A skin lesion imaged with a dermatoscope.
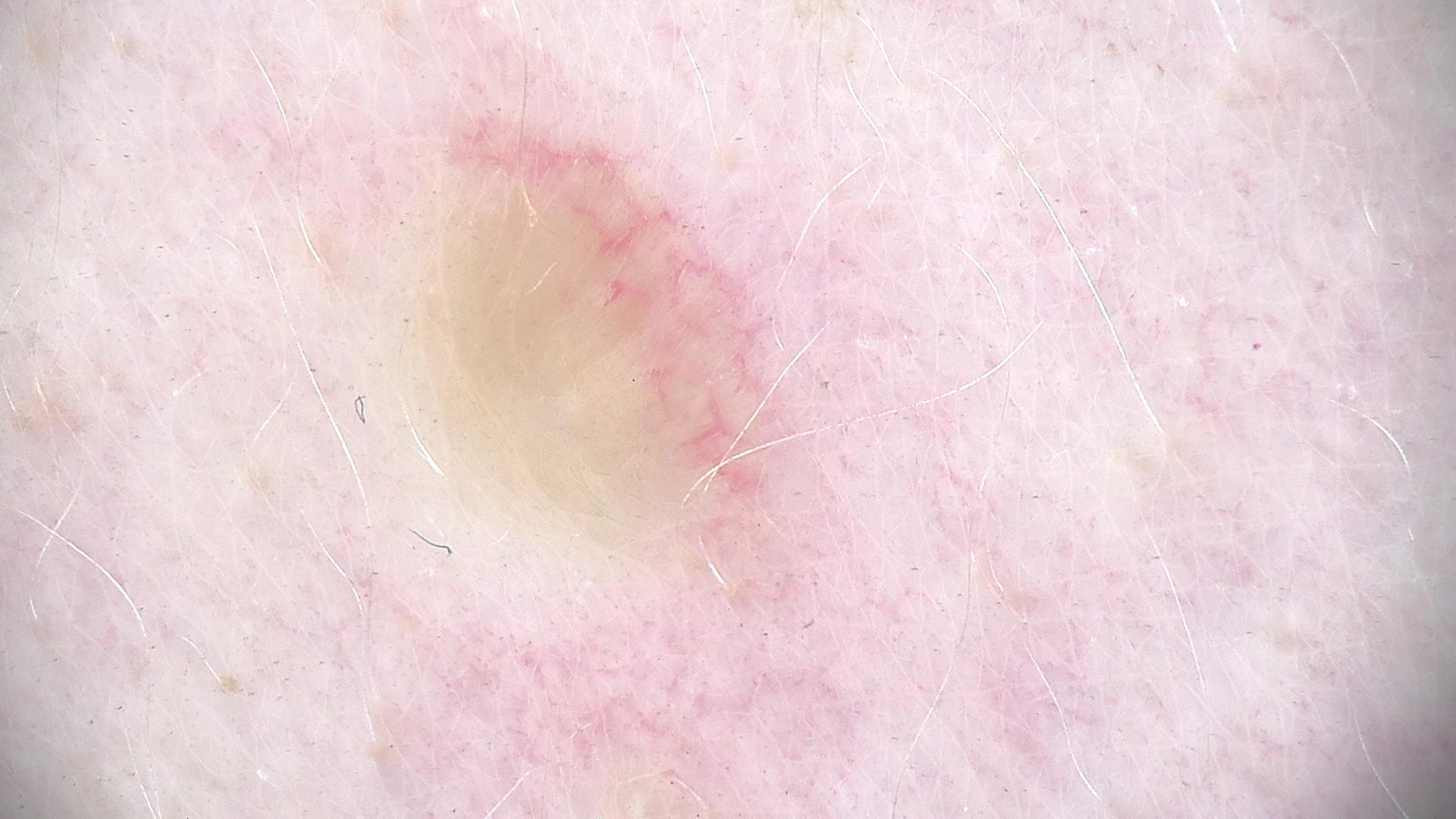The diagnosis was a banal lesion — a dermal nevus.